A dermoscopic close-up of a skin lesion.
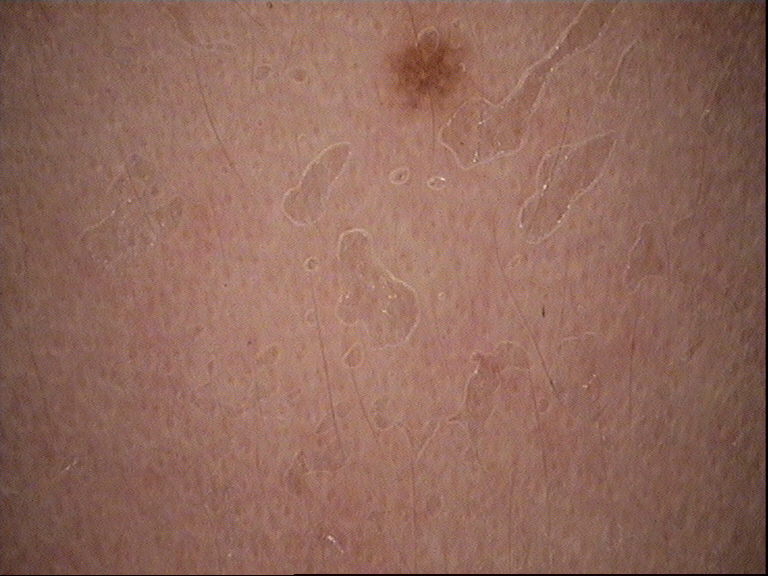Conclusion:
Consistent with a dysplastic junctional nevus.